A dermoscopic close-up of a skin lesion: 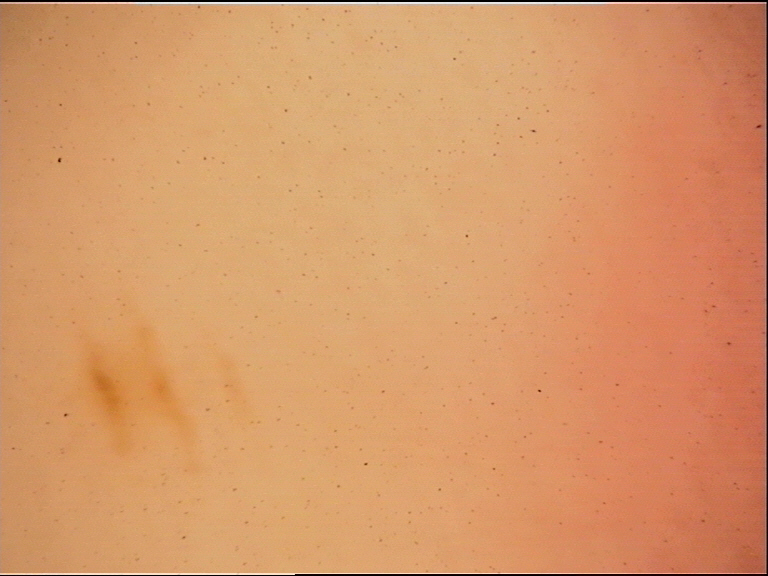Conclusion: Classified as a banal lesion — an acral junctional nevus.